The patient is 18–29, male. An image taken at an angle.
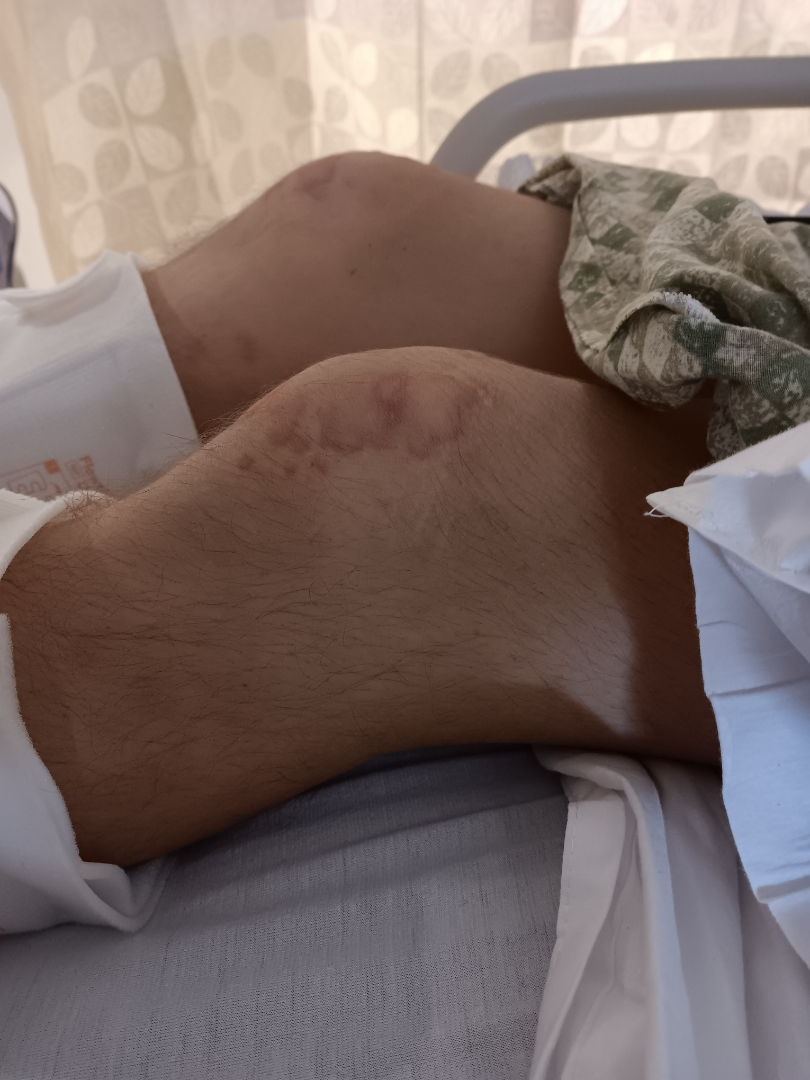Q: How does the patient describe it?
A: a rash
Q: How long has this been present?
A: about one day
Q: How does the lesion feel?
A: raised or bumpy
Q: Fitzpatrick or Monk tone?
A: FST II; lay reviewers estimated Monk skin tone scale 2 or 4
Q: What symptoms does the patient report?
A: none reported
Q: What conditions are considered?
A: three dermatologists independently reviewed the case: favoring Rheumatoid nodule; with consideration of gouty tophi; an alternative is Granuloma annulare